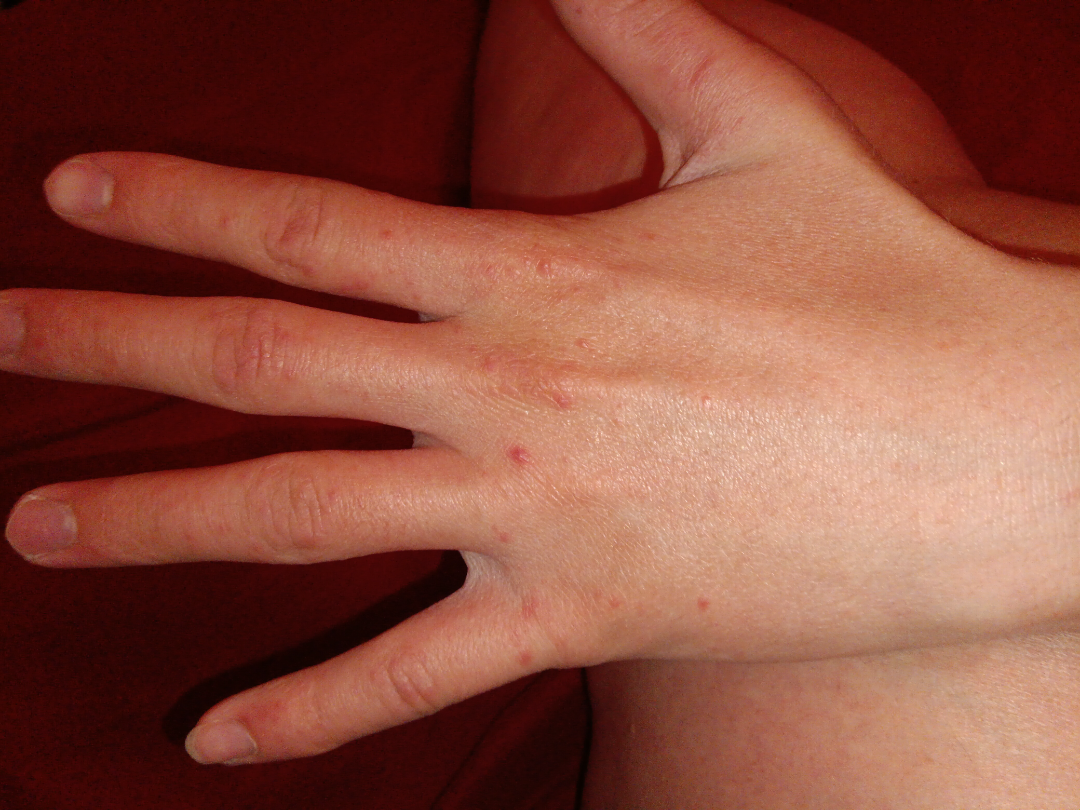Q: How was the photo taken?
A: close-up
Q: What conditions are considered?
A: the differential, in no particular order, includes Scabies and Eczema